The arm and sole of the foot are involved. Texture is reported as fluid-filled and rough or flaky. The contributor is 18–29, male. The patient described the issue as a rash. Reported lesion symptoms include bleeding, itching and burning. The contributor notes associated mouth sores. The condition has been present for less than one week. This image was taken at a distance — 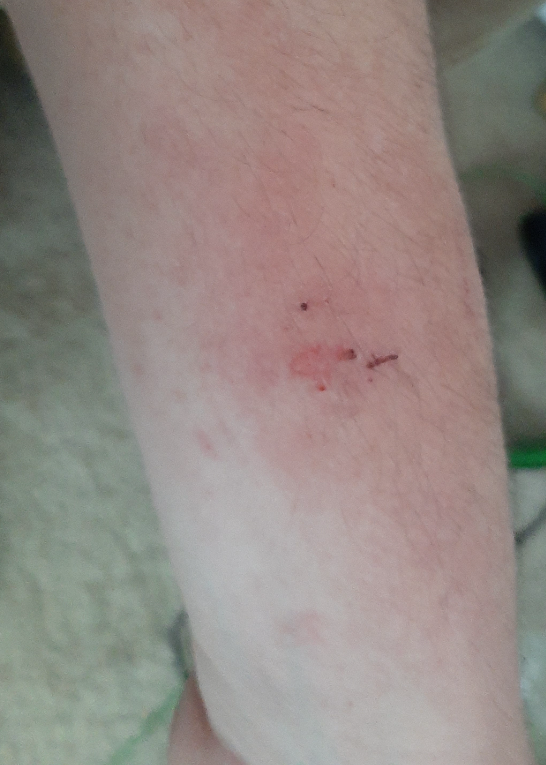Impression:
No differential diagnosis could be assigned on photographic review.